The photograph was taken at a distance; the arm is involved — 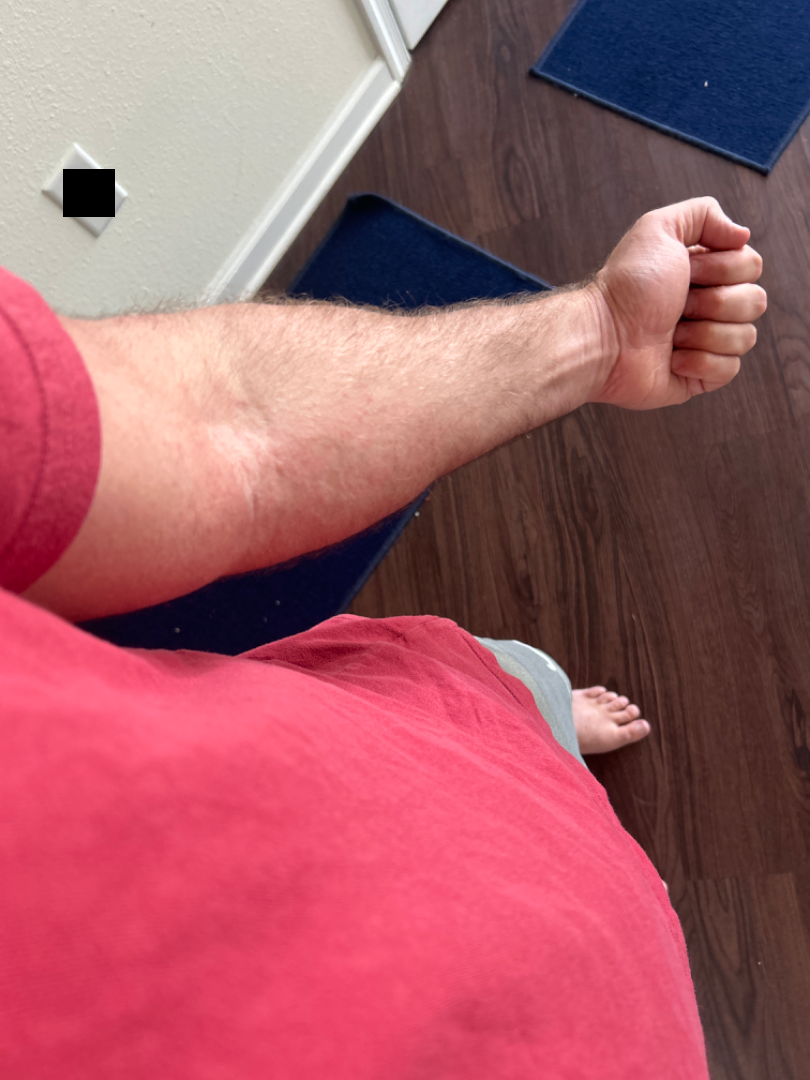Clinical context: The patient reported no systemic symptoms. The patient considered this a rash. Assessment: On teledermatology review: most likely Eczema; also on the differential is Contact dermatitis, NOS; a remote consideration is Viral Exanthem.